This is a dermoscopic photograph of a skin lesion. A male patient, aged approximately 45 — 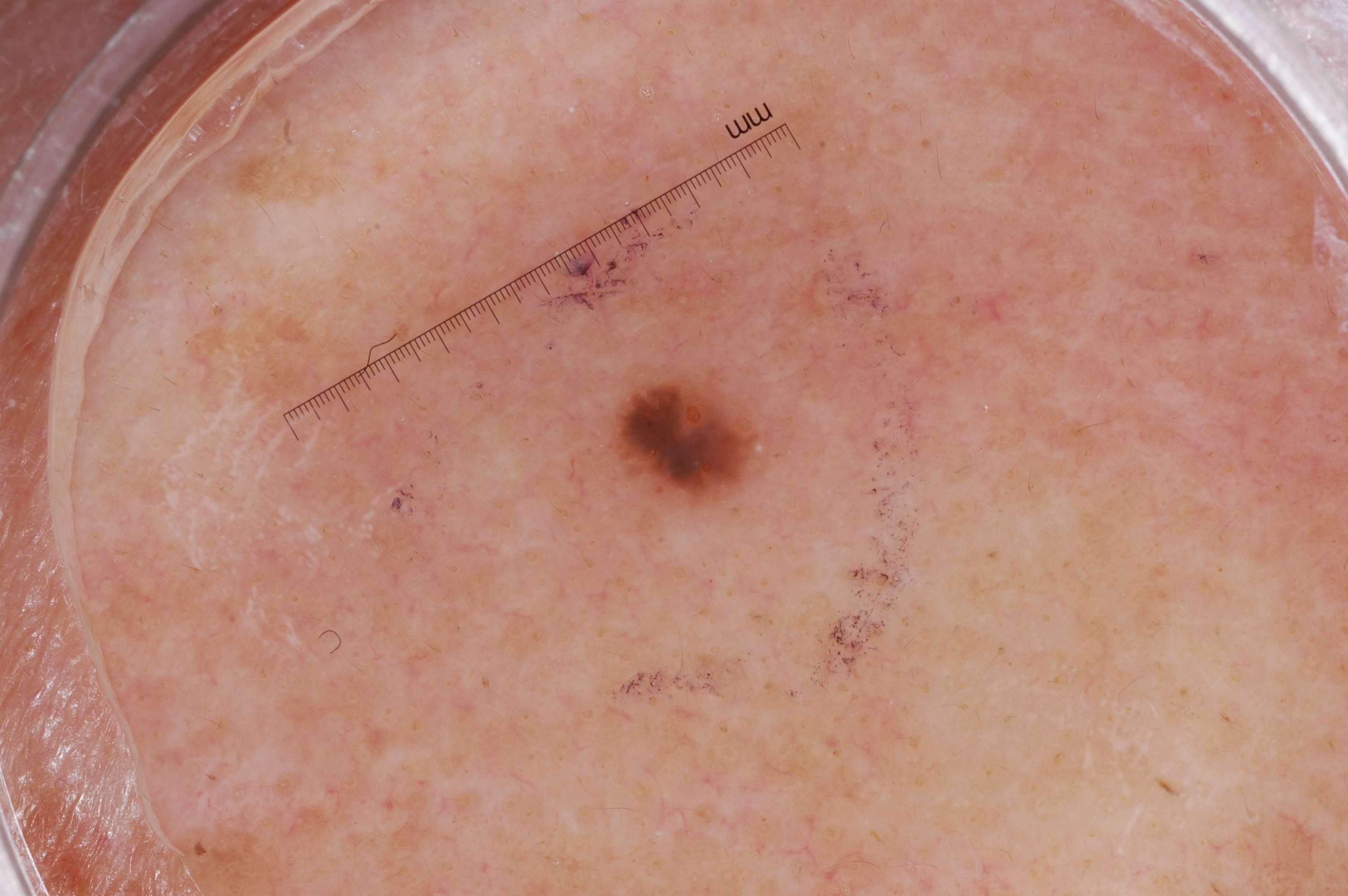{
  "lesion_location": {
    "bbox_xyxy": [
      606,
      373,
      770,
      516
    ]
  },
  "dermoscopic_features": {
    "present": [
      "milia-like cysts"
    ],
    "absent": [
      "negative network",
      "pigment network",
      "streaks"
    ]
  },
  "diagnosis": {
    "name": "seborrheic keratosis",
    "malignancy": "benign",
    "lineage": "keratinocytic",
    "provenance": "clinical"
  }
}